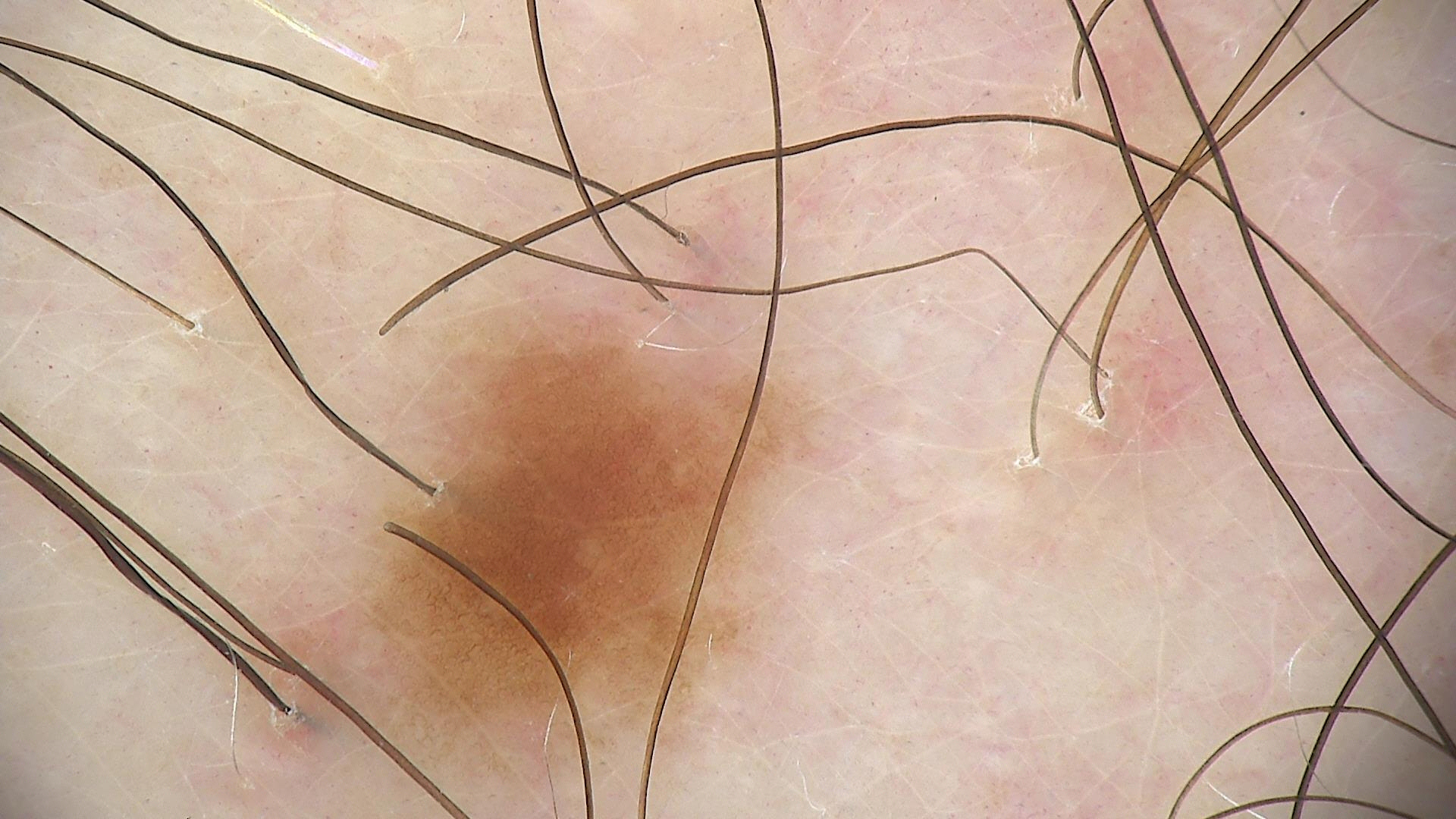The diagnostic label was a junctional nevus.